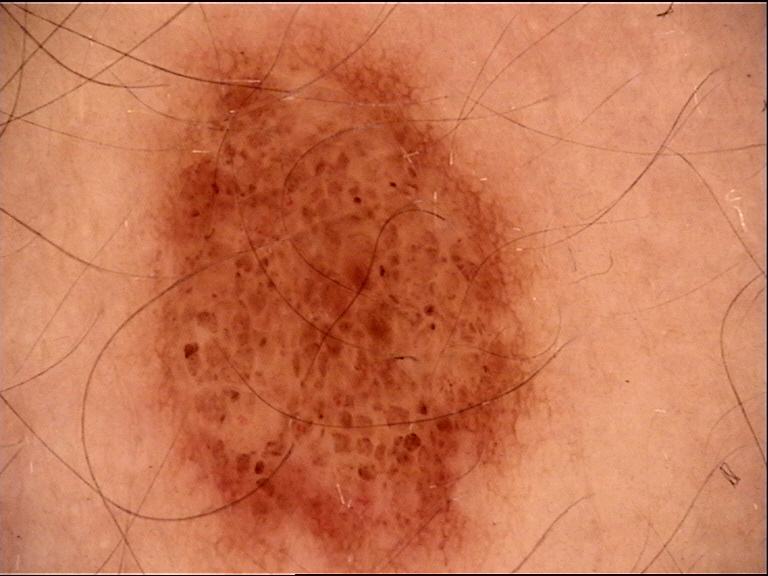Impression: The diagnostic label was a banal lesion — a junctional nevus.